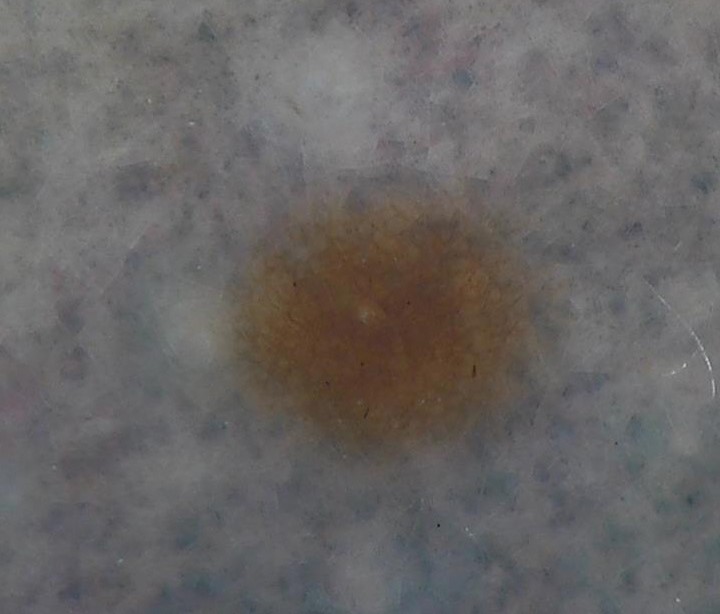<case>
  <image>dermoscopy</image>
  <diagnosis>
    <name>dysplastic junctional nevus</name>
    <code>jd</code>
    <malignancy>benign</malignancy>
    <super_class>melanocytic</super_class>
    <confirmation>expert consensus</confirmation>
  </diagnosis>
</case>